The contributor reports the lesion is flat and raised or bumpy · the photo was captured at a distance: 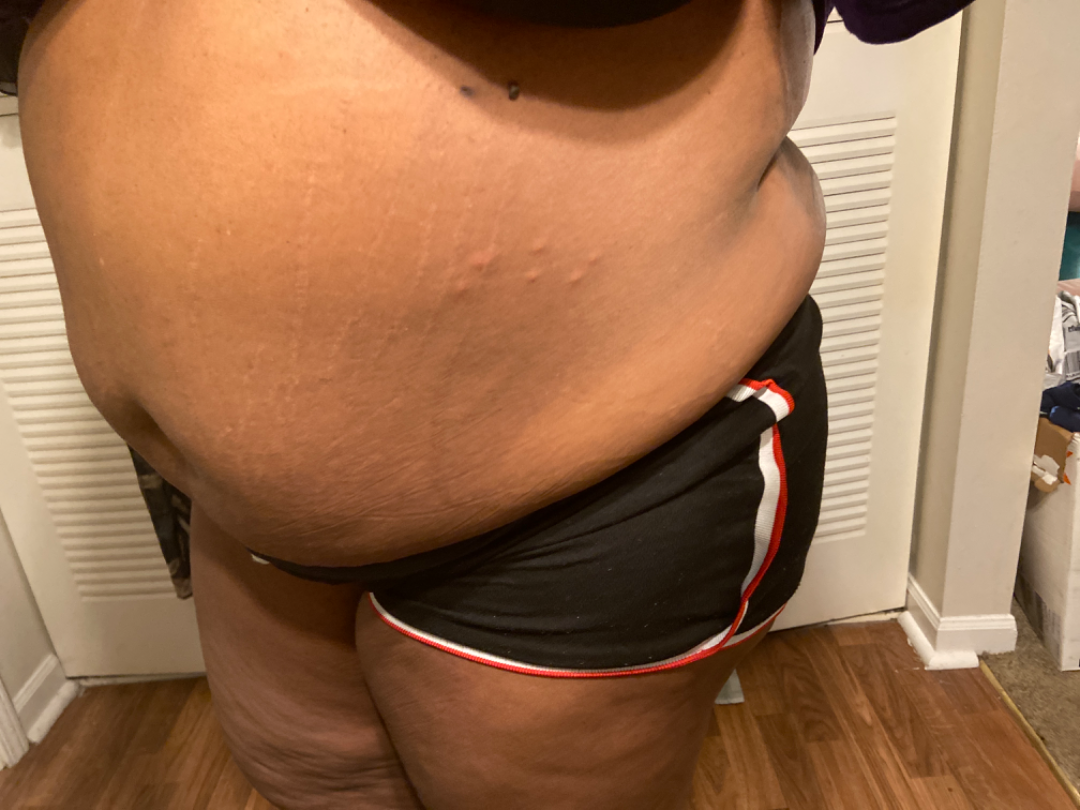The image was not sufficient for the reviewer to characterize the skin condition.